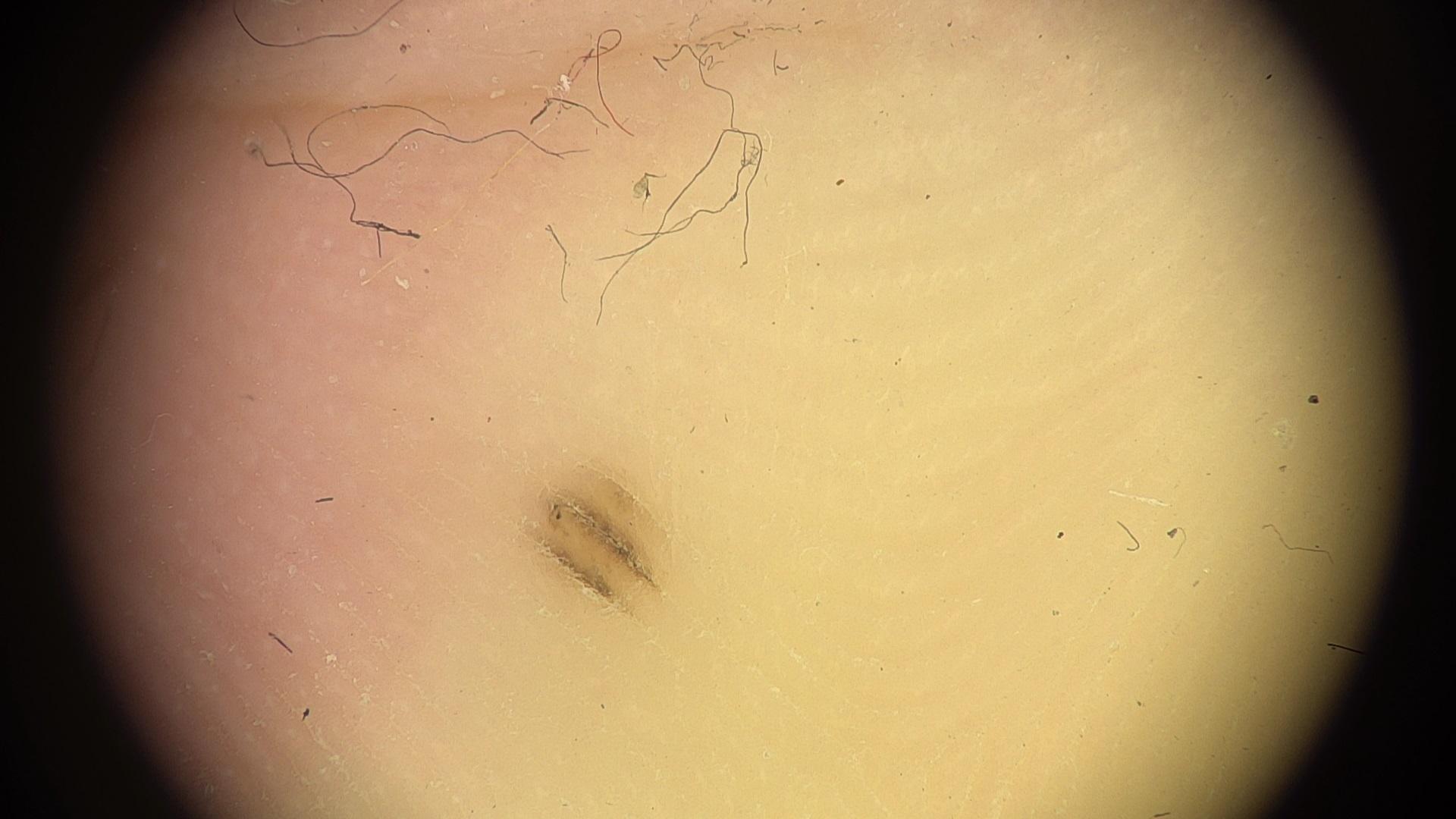subject = female, aged 23-27 | imaging = dermoscopy | skin phototype = II | location = an acral site (palms or soles) | diagnosis = Nevus (clinical impression).